Female subject, age 40–49 · the lesion involves the arm · an image taken at an angle.
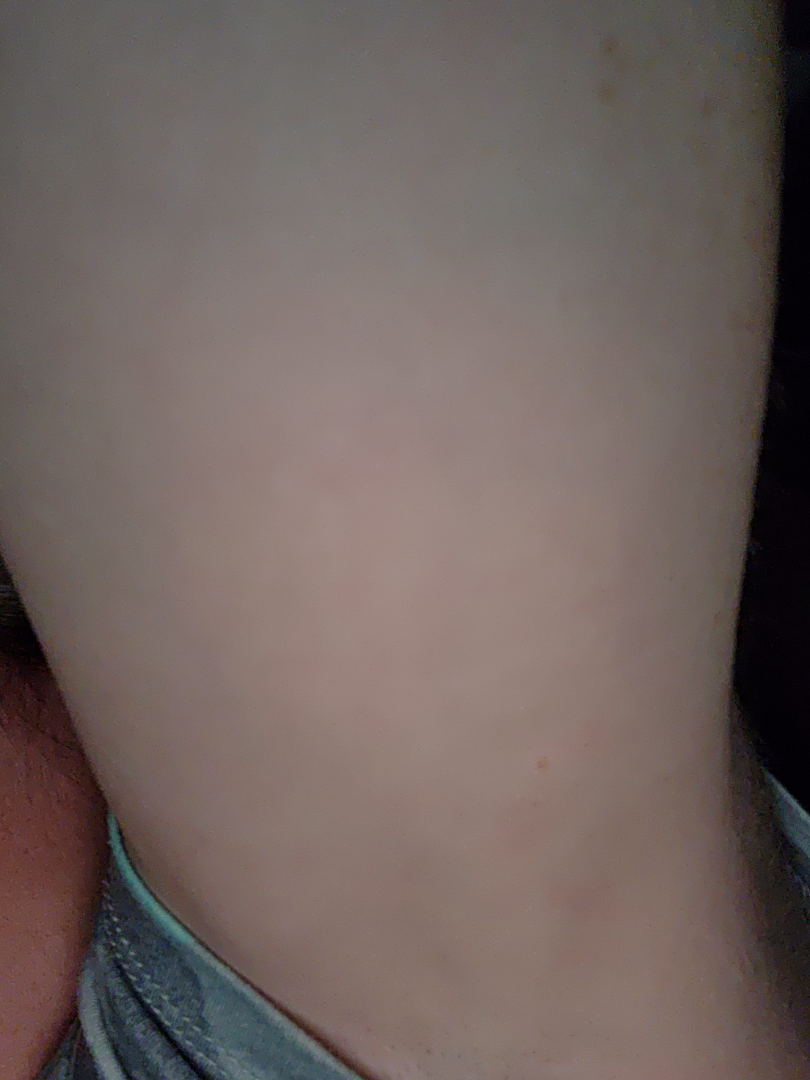| field | value |
|---|---|
| assessment | no clear pathology |